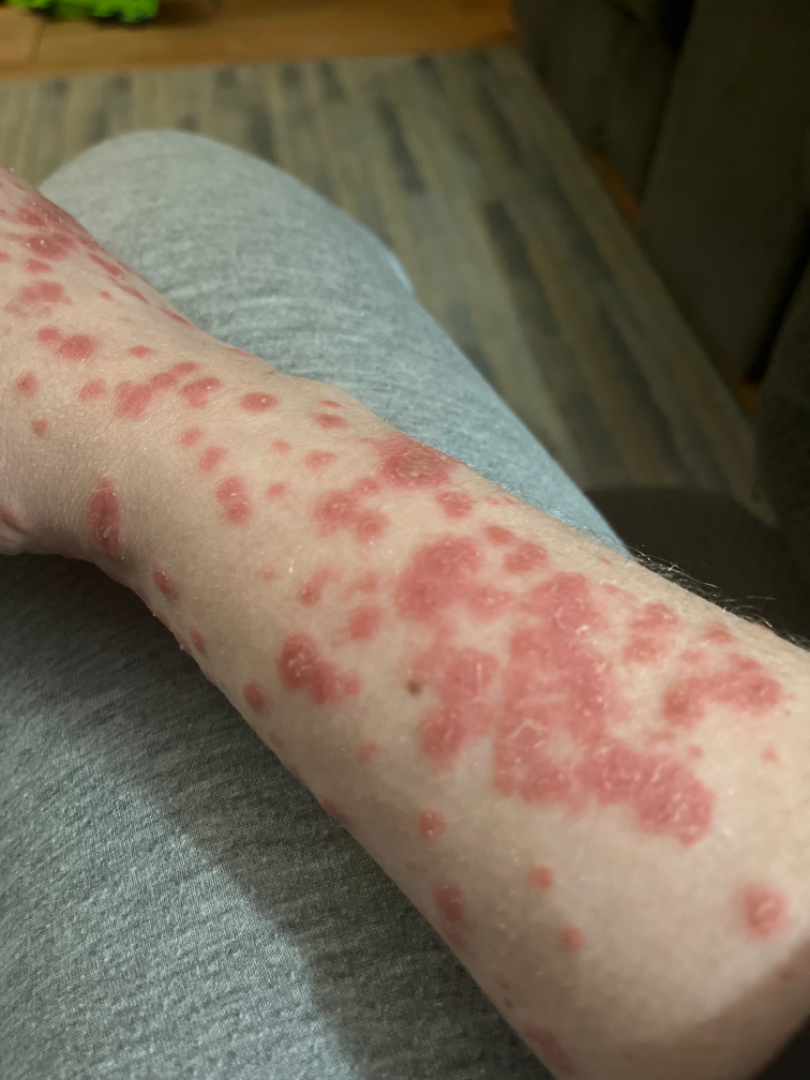The photo was captured at an angle.
On dermatologist assessment of the image: Erythema multiforme (favored).